The referring clinician suspected melanoma. A female patient aged 50. The patient describes having a moderate number of moles.
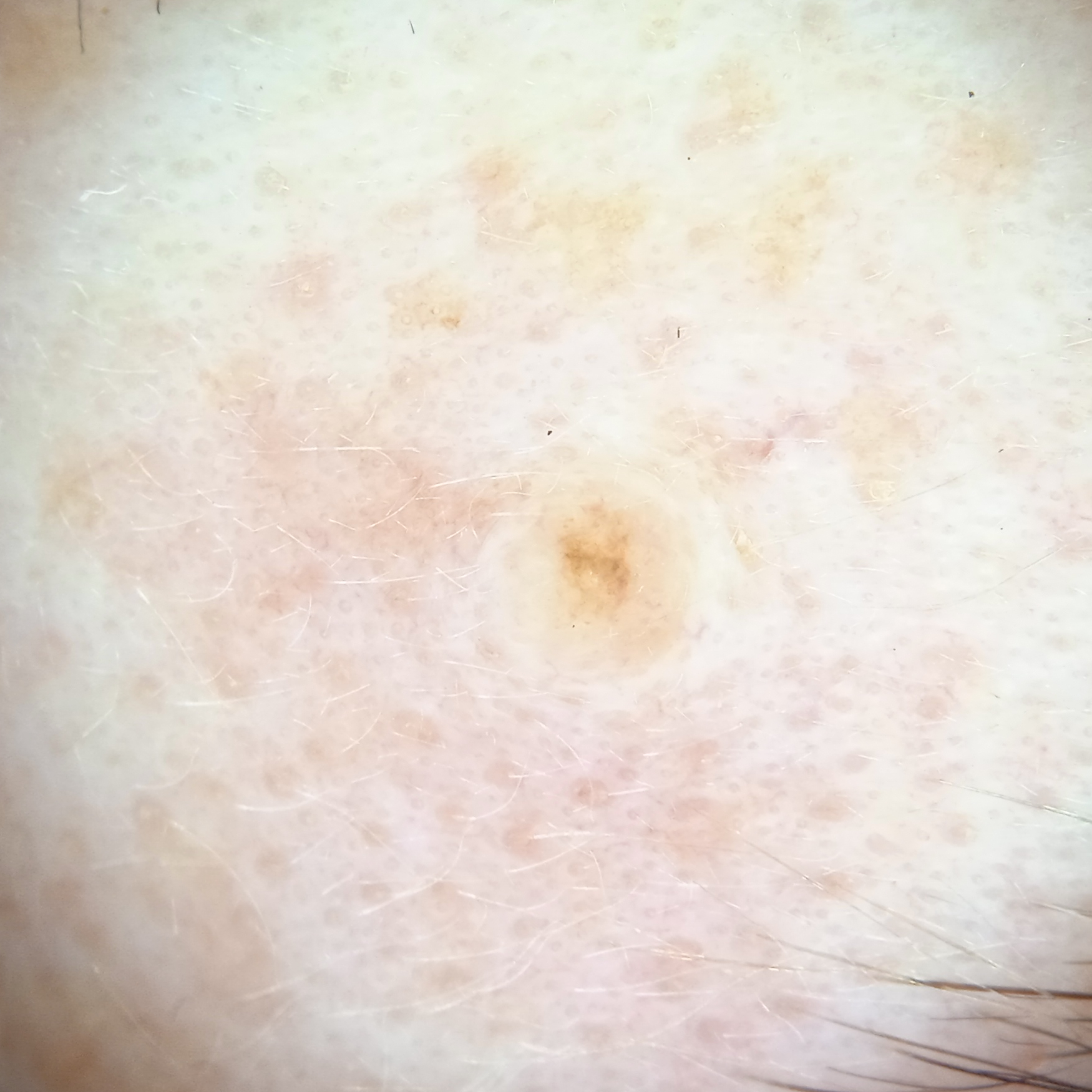Located on the face. The lesion is about 1.8 mm across. The lesion was assessed as a melanocytic nevus.